The photo was captured at an angle. Located on the leg. The subject is a female aged 50–59:
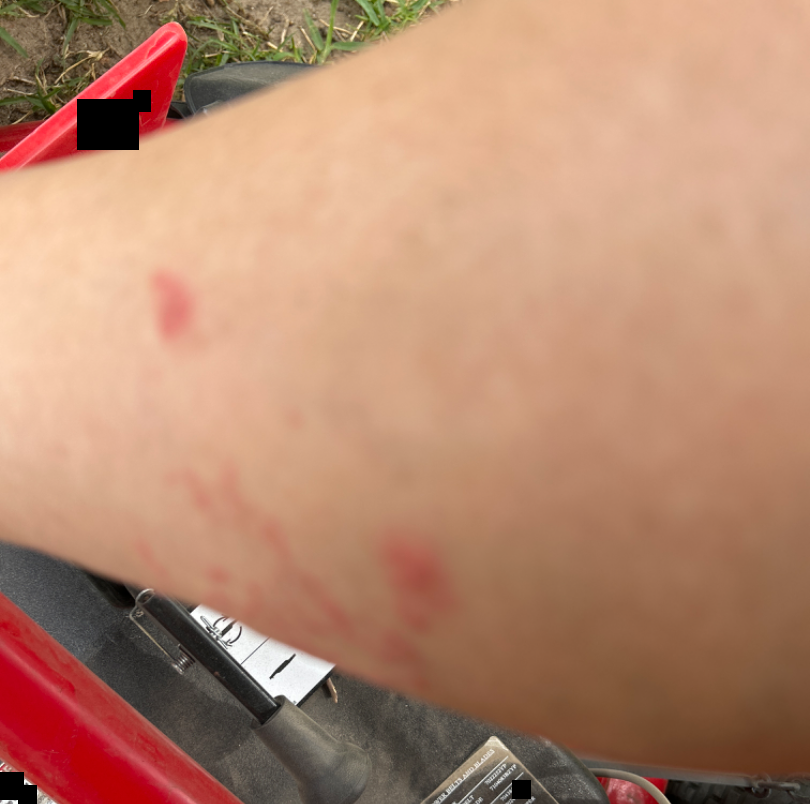Reviewed remotely by one dermatologist: the differential includes Eczema and Allergic Contact Dermatitis, with no clear leading consideration; less likely is Psoriasis.